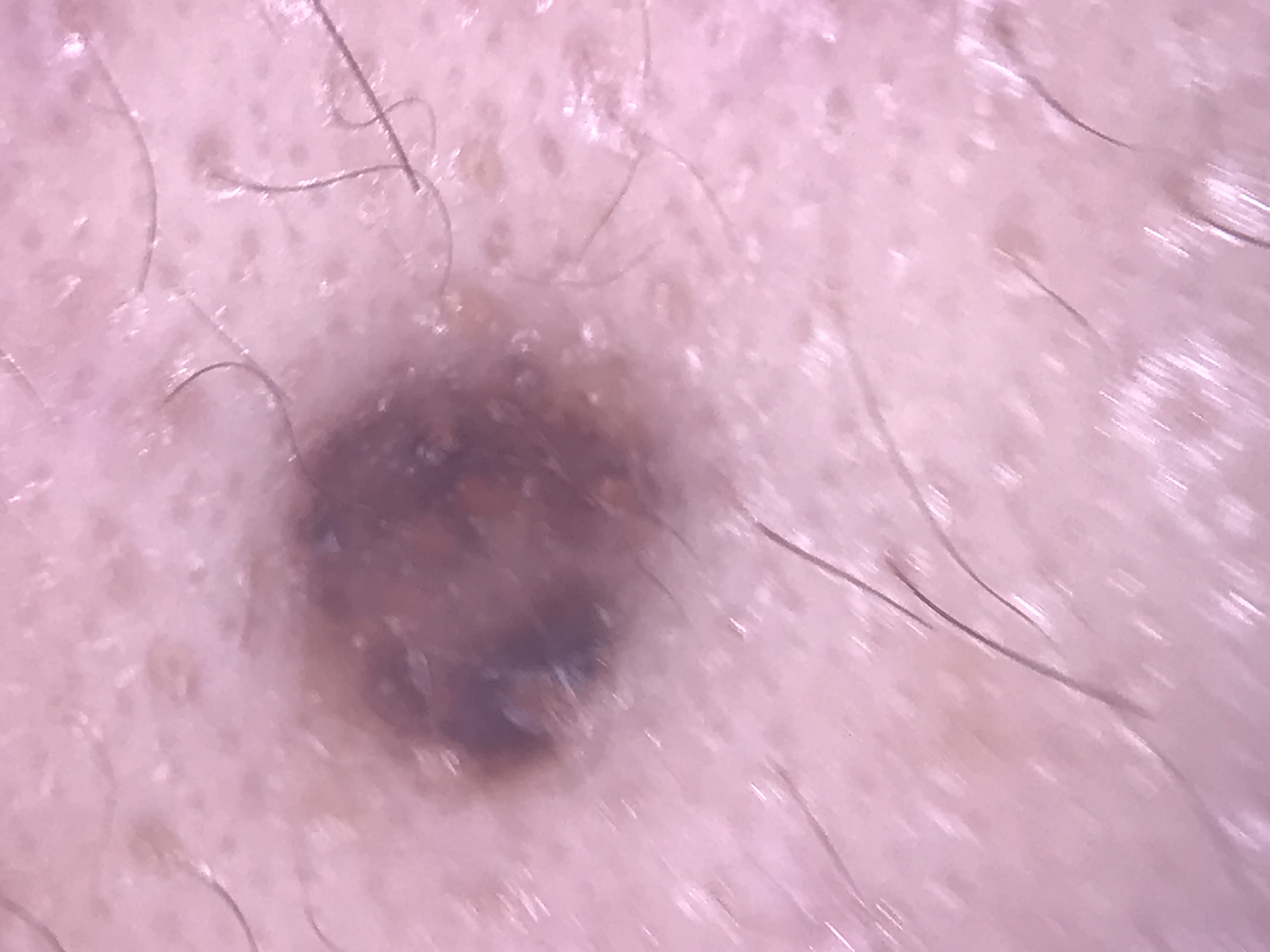image type = dermoscopy; subtype = banal; diagnosis = compound nevus (expert consensus).